The lesion involves the leg · the photo was captured at a distance · the contributor is a female aged 30–39:
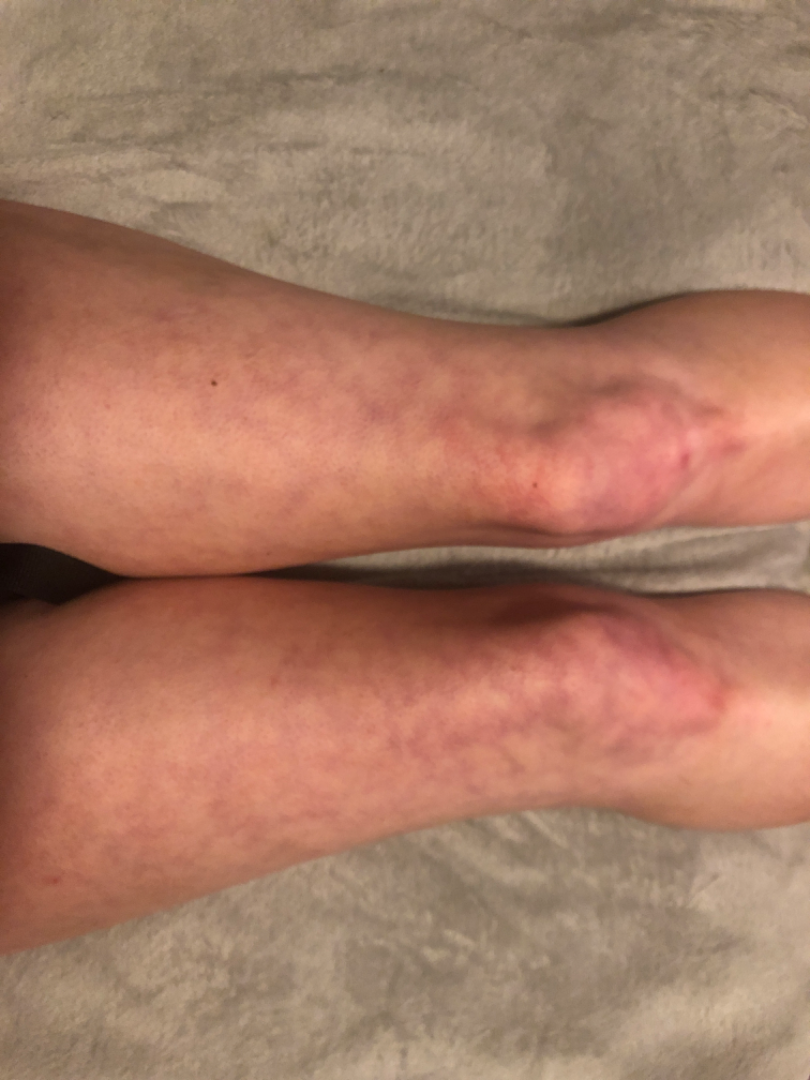History:
Skin tone: FST IV; lay graders estimated Monk Skin Tone 3 or 4 (two reviewer pools). The lesion is described as flat. The lesion is associated with bothersome appearance. The contributor notes the condition has been present for more than five years.
Impression:
Three dermatologists independently reviewed the case: the impression was split between Livedo reticularis and Erythema ab igne.